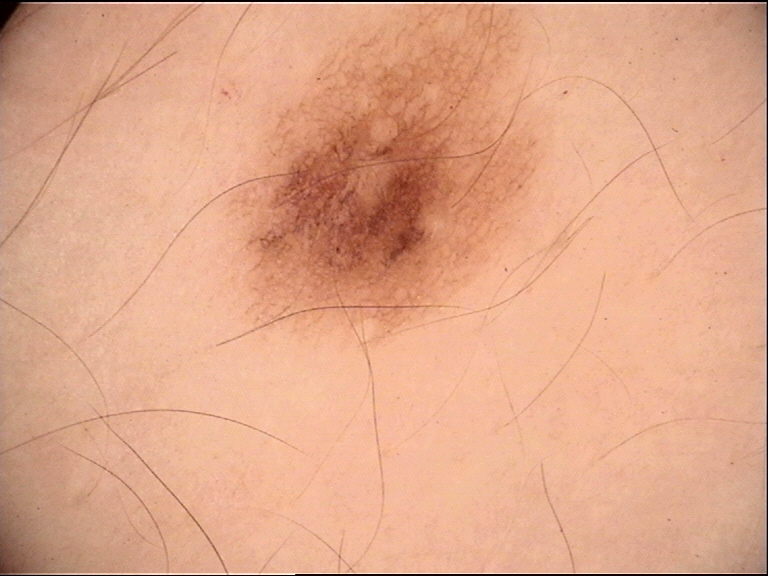Findings: A dermoscopic image of a skin lesion. Impression: Diagnosed as a dysplastic junctional nevus.